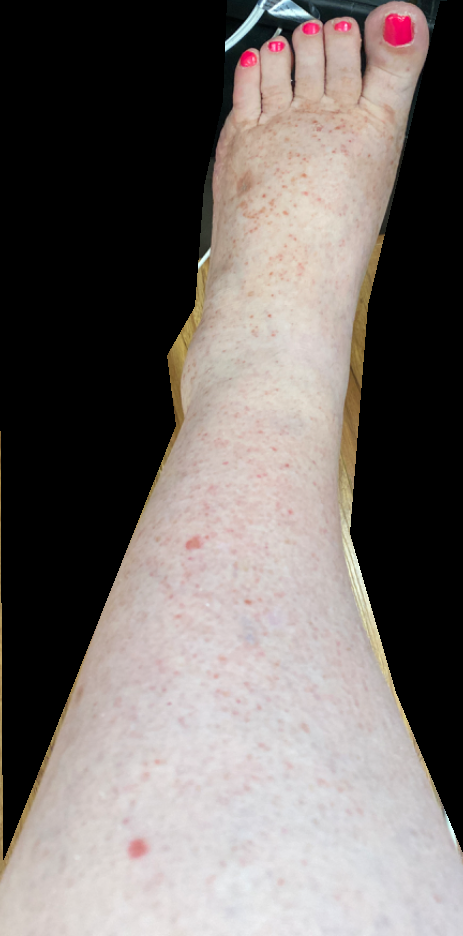Clinical context: Present for one to three months. The affected area is the top or side of the foot and leg. The patient reports associated joint pain, fatigue and shortness of breath. The lesion is associated with bothersome appearance and itching. An image taken at a distance. The lesion is described as raised or bumpy. Assessment: On photographic review: Pigmented purpuric eruption (considered); Leukocytoclastic Vasculitis (considered).